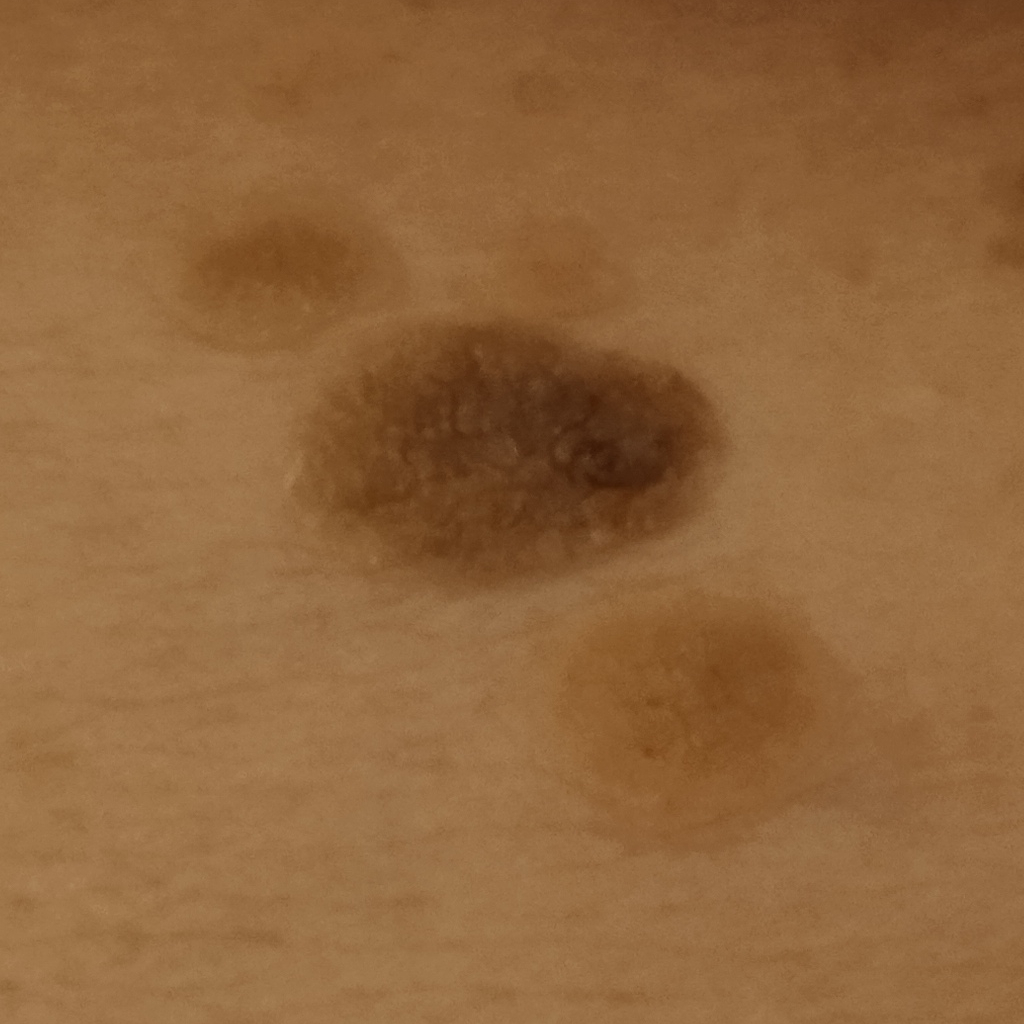The patient says their skin reddens painfully with sun exposure.
Imaged for a research study, with no referral diagnosis recorded.
The patient describes having a moderate number of moles.
The lesion is on the torso.
The lesion measures approximately 12.2 mm.
The consensus diagnosis for this lesion was a seborrheic keratosis.